The photograph is a close-up of the affected area:
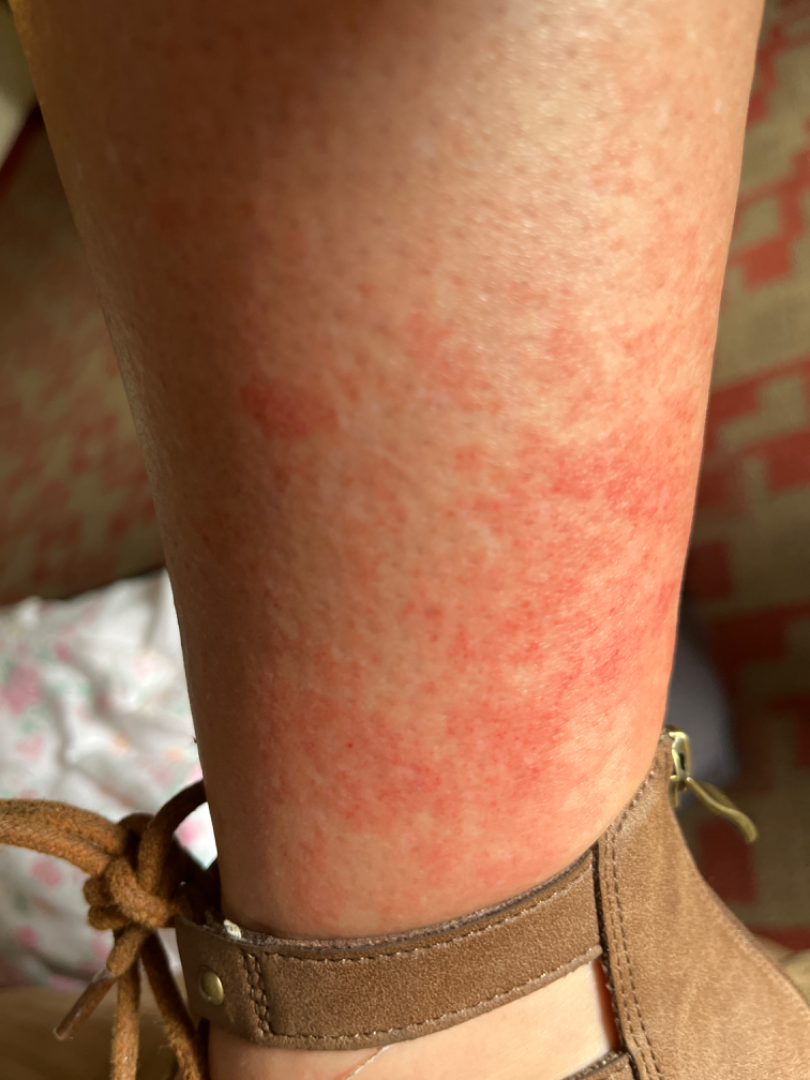Impression:
The case was difficult to assess from the available photograph.